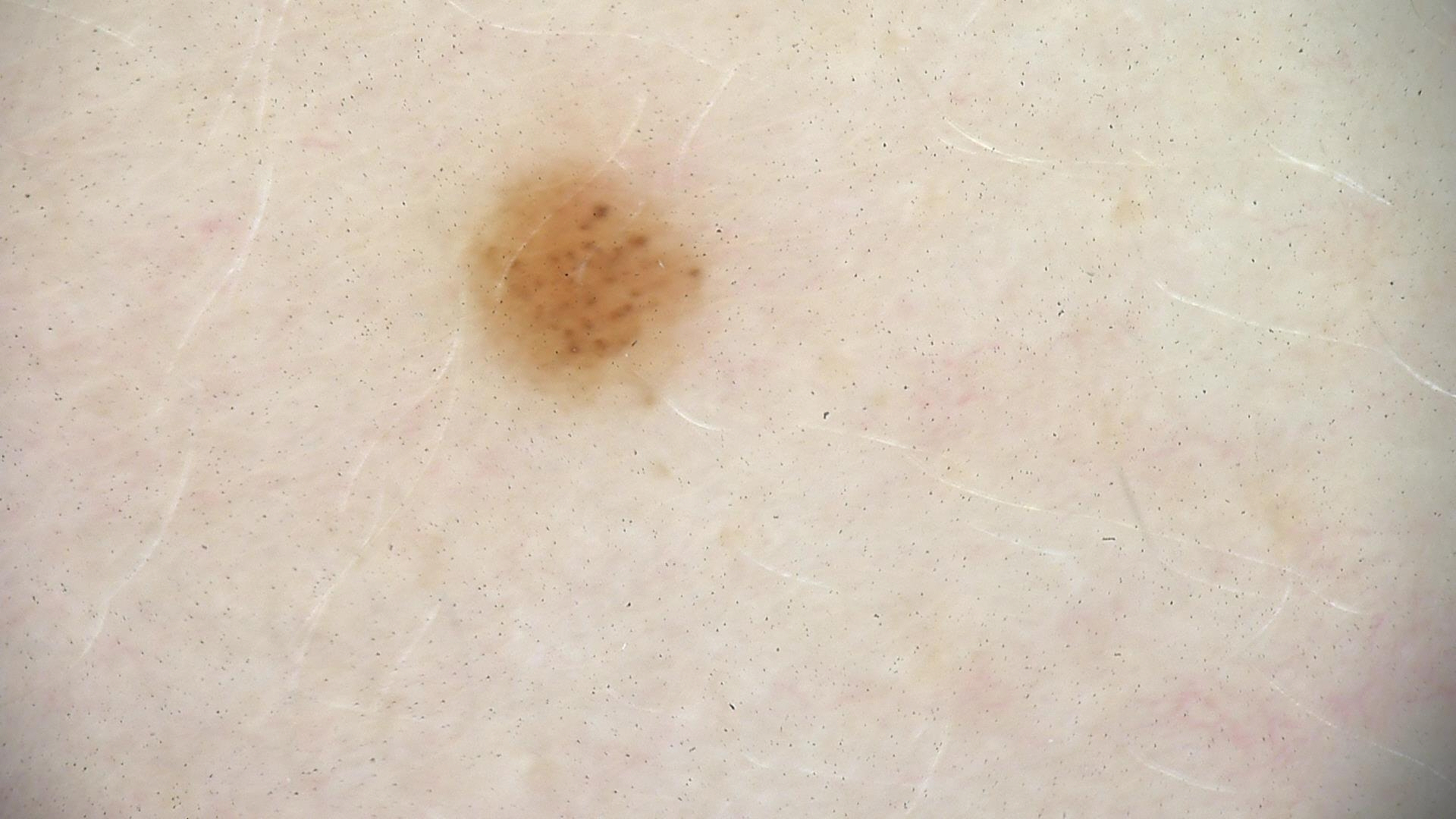Consistent with a dysplastic junctional nevus.